Dermoscopy of a skin lesion, the subject is a female aged 78-82:
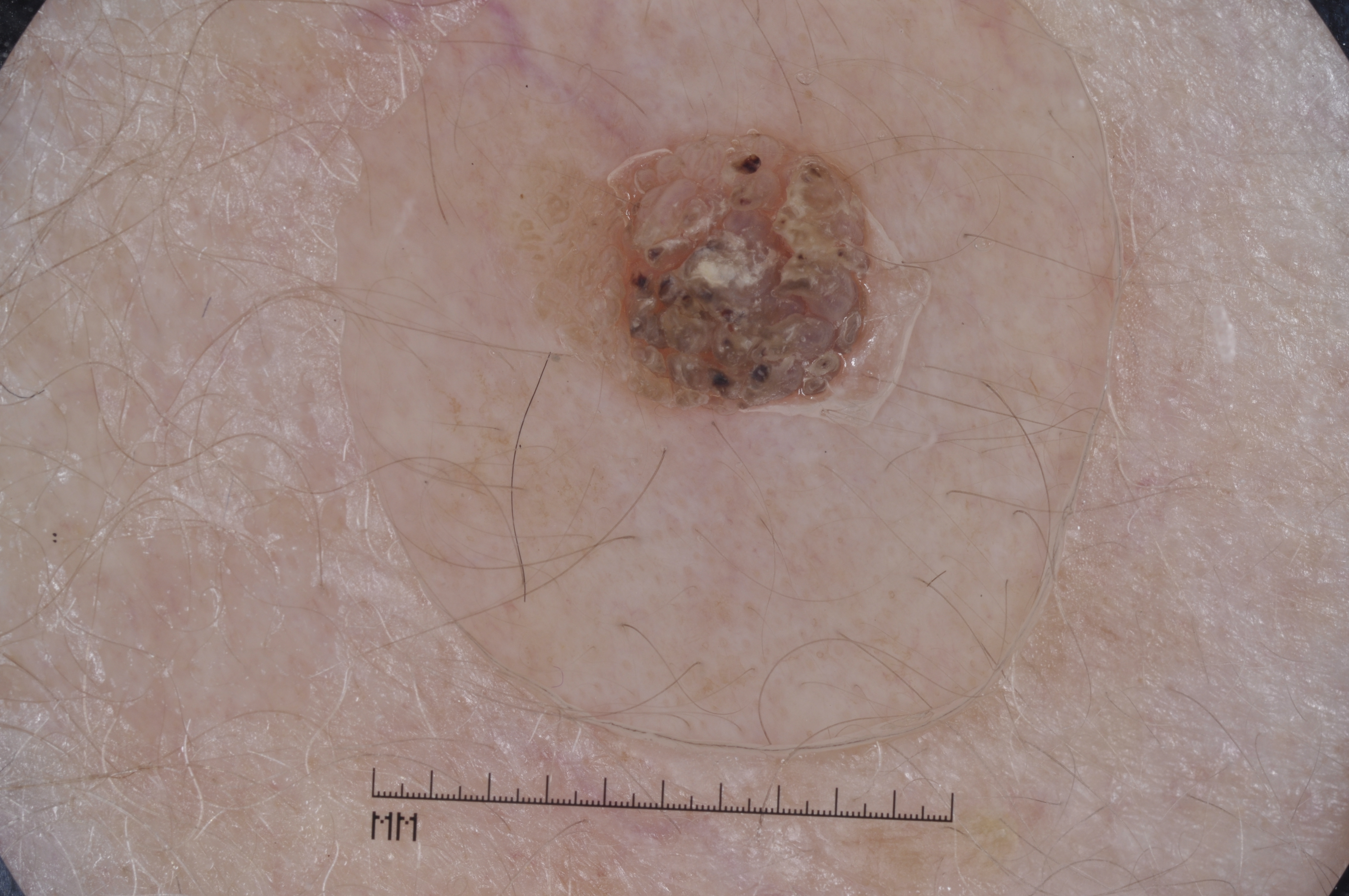Dermoscopic examination shows milia-like cysts.
The lesion is small relative to the field of view.
The lesion is located at x1=527, y1=126, x2=885, y2=420.
Diagnosed as a seborrheic keratosis.